A dermoscopic close-up of a skin lesion.
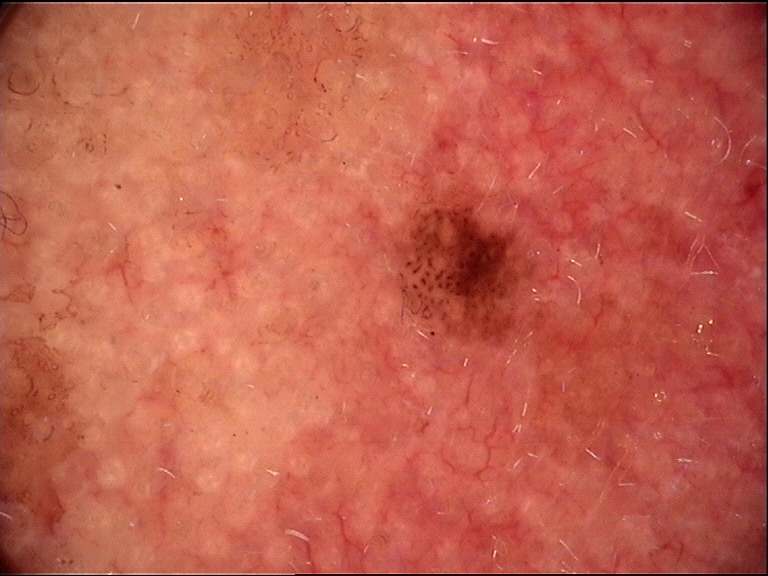The diagnostic label was a dysplastic junctional nevus.